A dermoscopic image of a skin lesion:
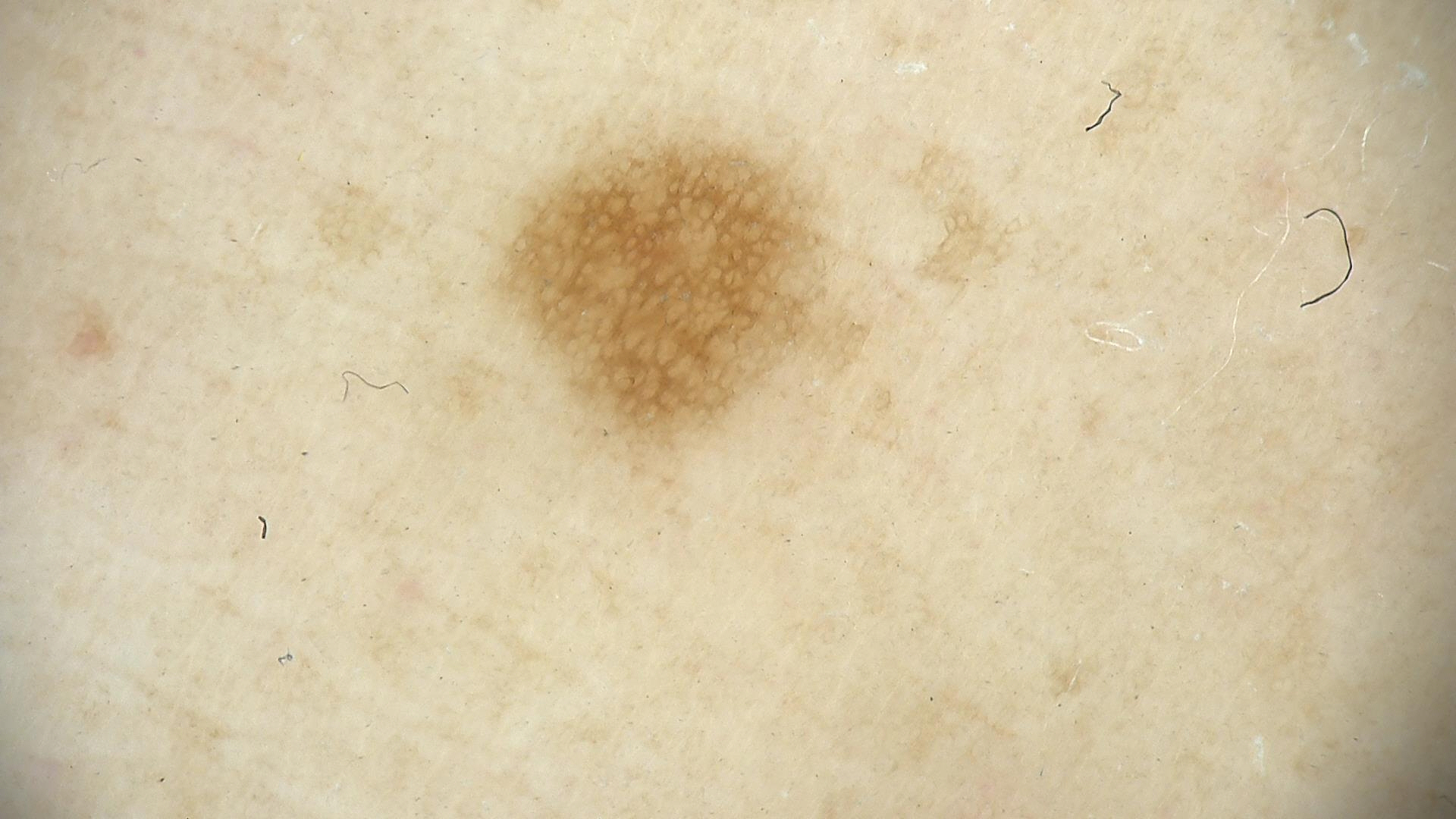Impression: Classified as a banal lesion — a junctional nevus.